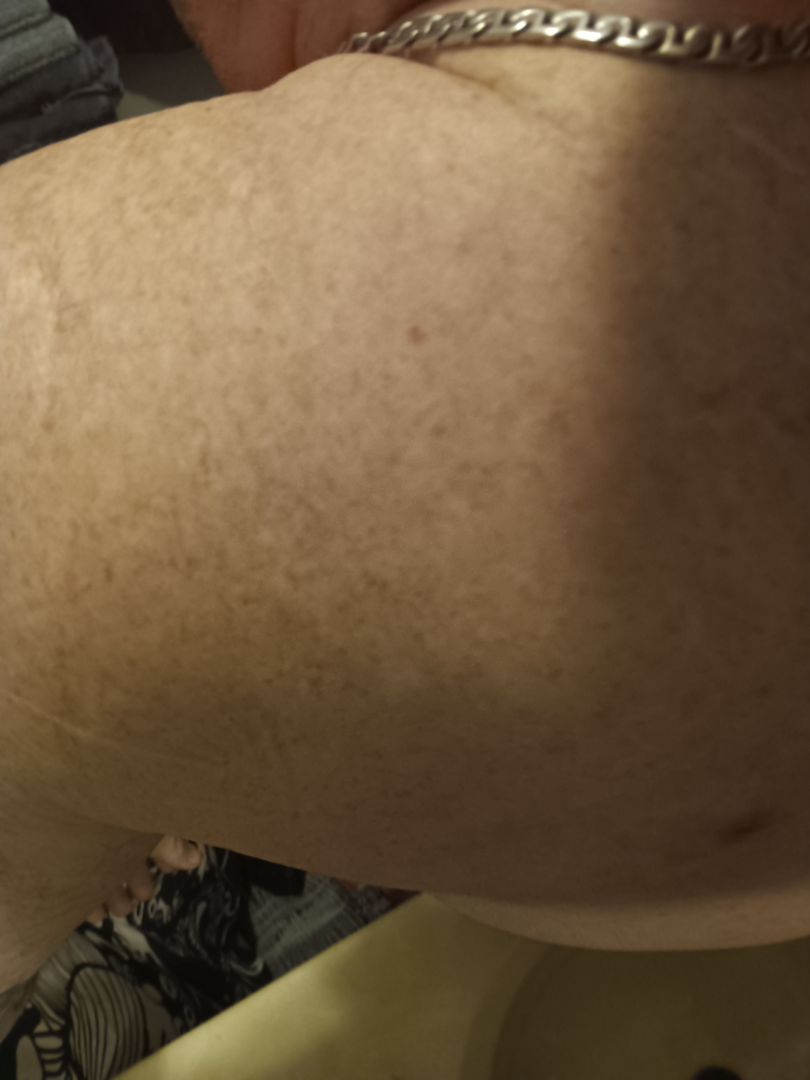{"shot_type": "at a distance", "symptoms": ["itching", "pain"], "systemic_symptoms": ["fatigue", "chills"], "patient": "male, age 50–59", "body_site": "back of the torso", "duration": "more than one year", "texture": "raised or bumpy"}